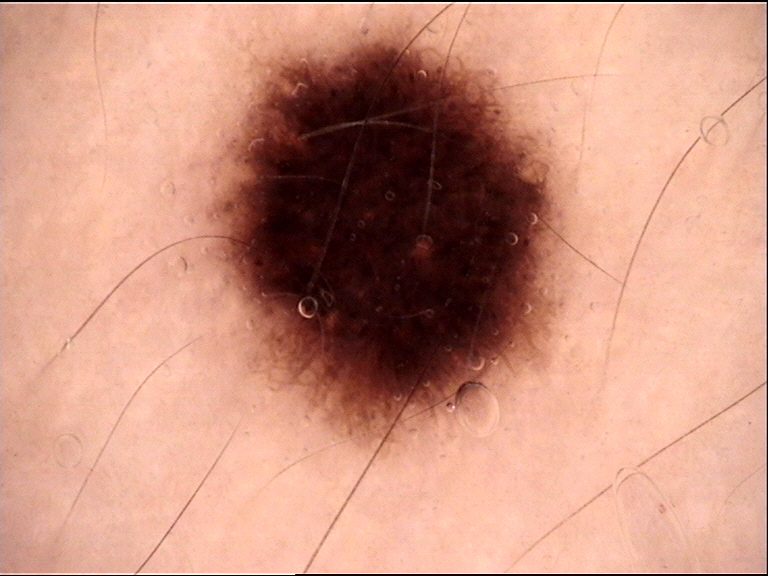The diagnostic label was a dysplastic junctional nevus.